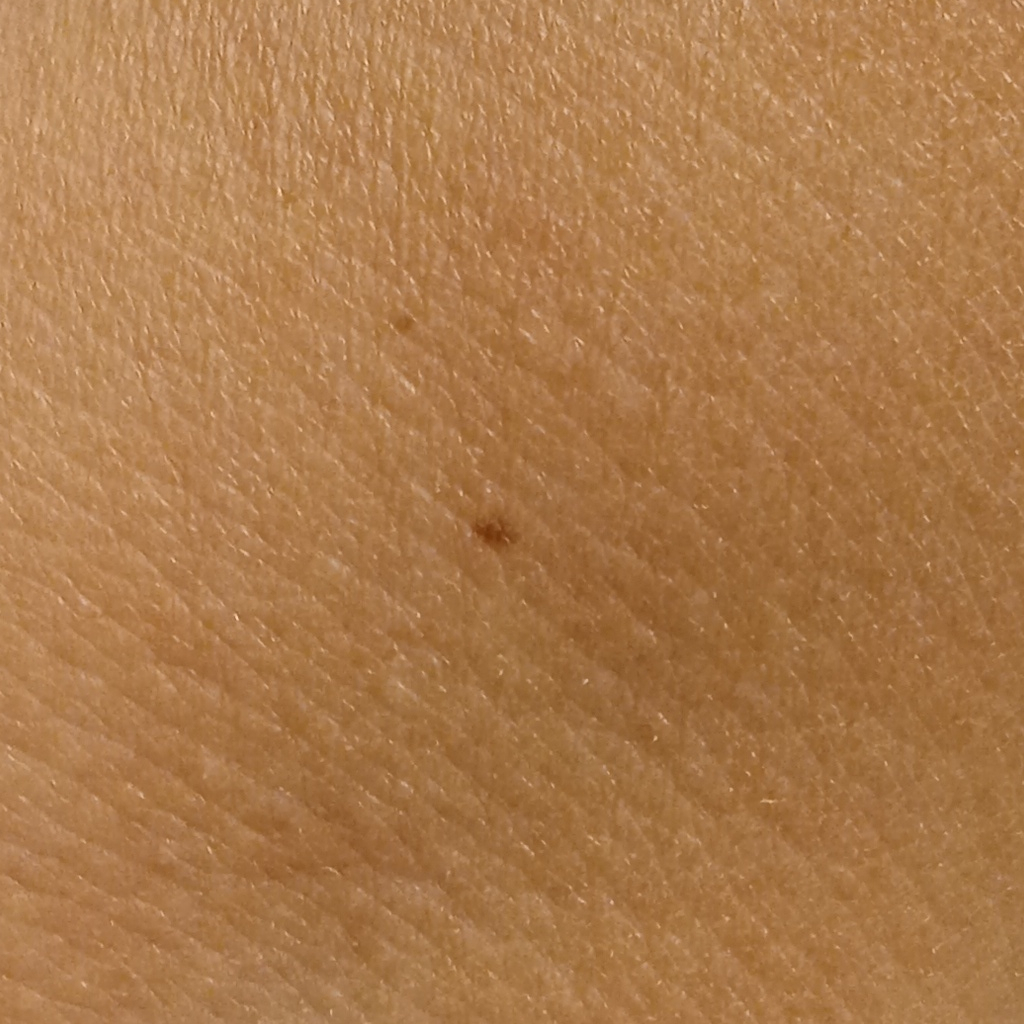{
  "image": "clinical photograph",
  "referral": "research study (no referral diagnosis)",
  "patient": {
    "age": 58,
    "sex": "female"
  },
  "lesion_location": "an arm",
  "lesion_size": {
    "diameter_mm": 1.9
  },
  "diagnosis": {
    "name": "melanocytic nevus",
    "malignancy": "benign"
  }
}